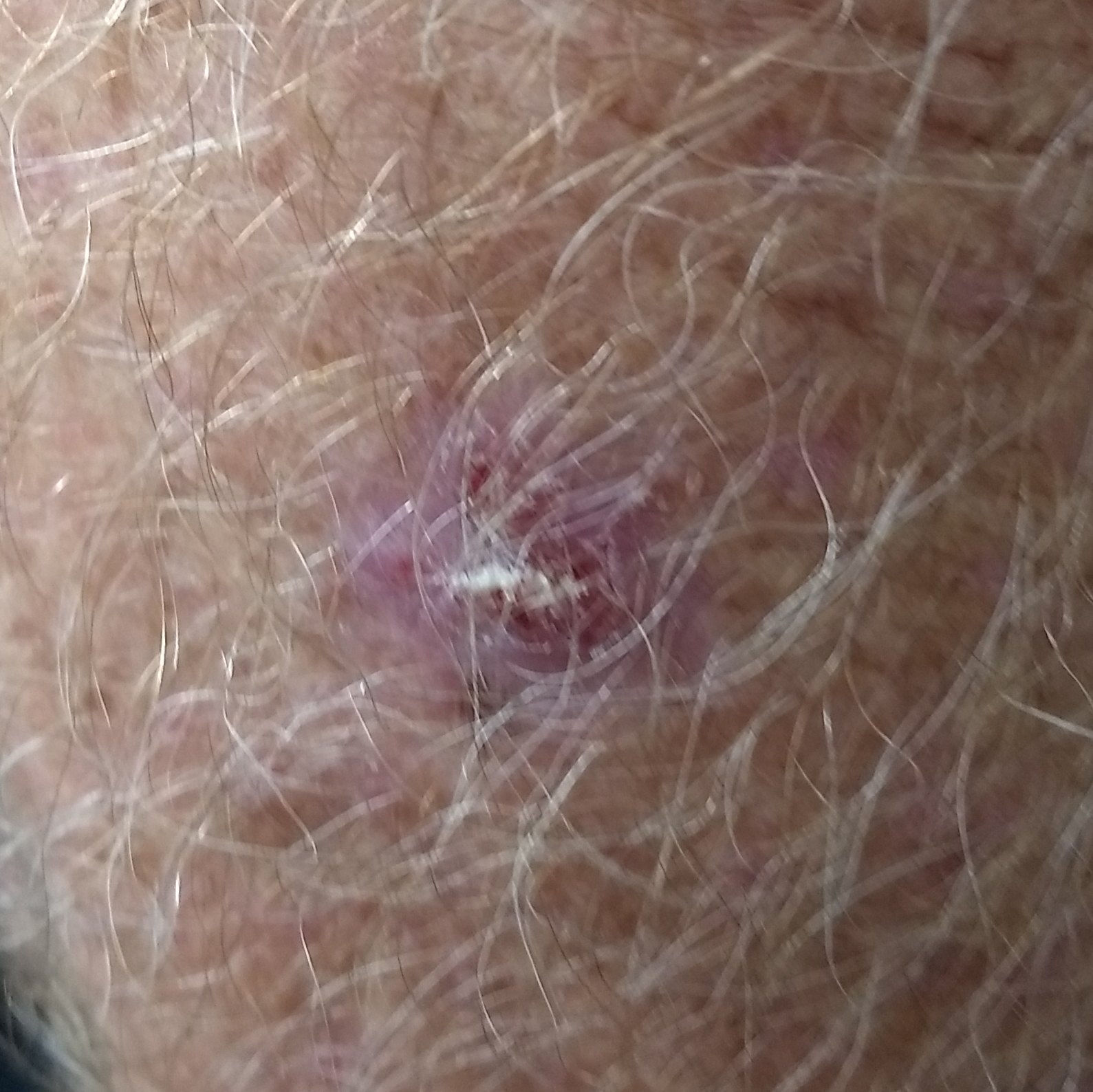– location · a forearm
– patient-reported symptoms · itching, elevation, bleeding / no pain
– diagnostic label · basal cell carcinoma (biopsy-proven)